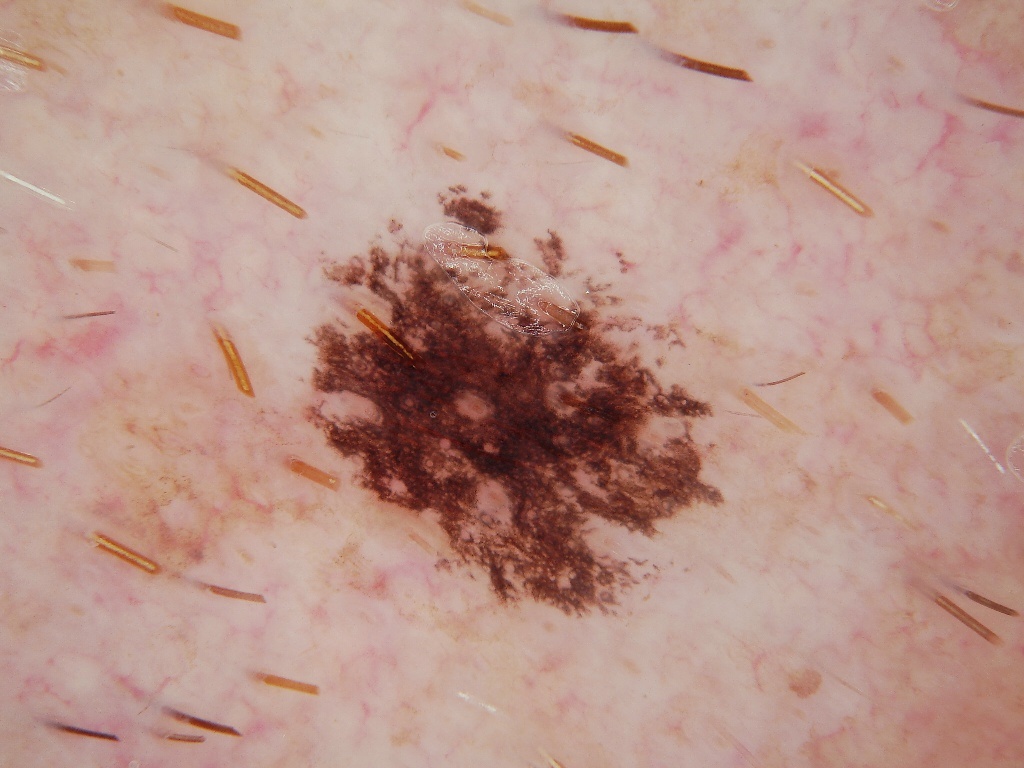modality: dermatoscopic image of a skin lesion
lesion location: x1=276, y1=172, x2=736, y2=637
size: moderate
absent dermoscopic features: streaks and globules
assessment: a benign lesion